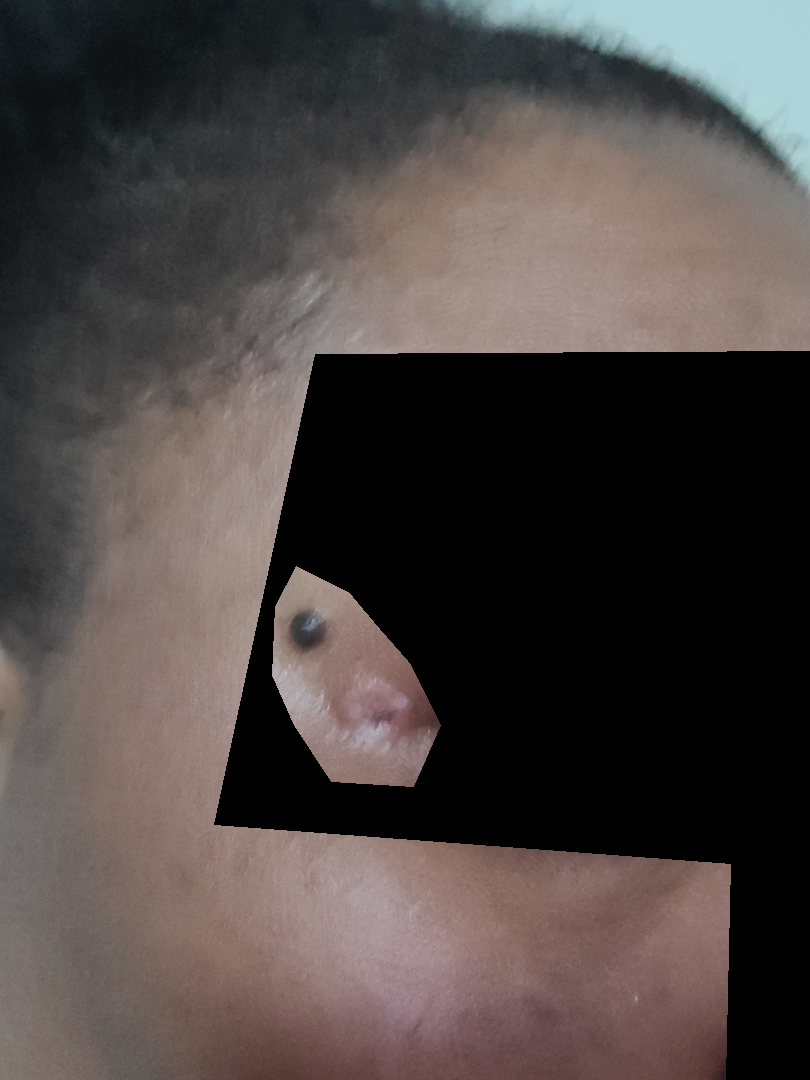assessment: indeterminate from the photograph.